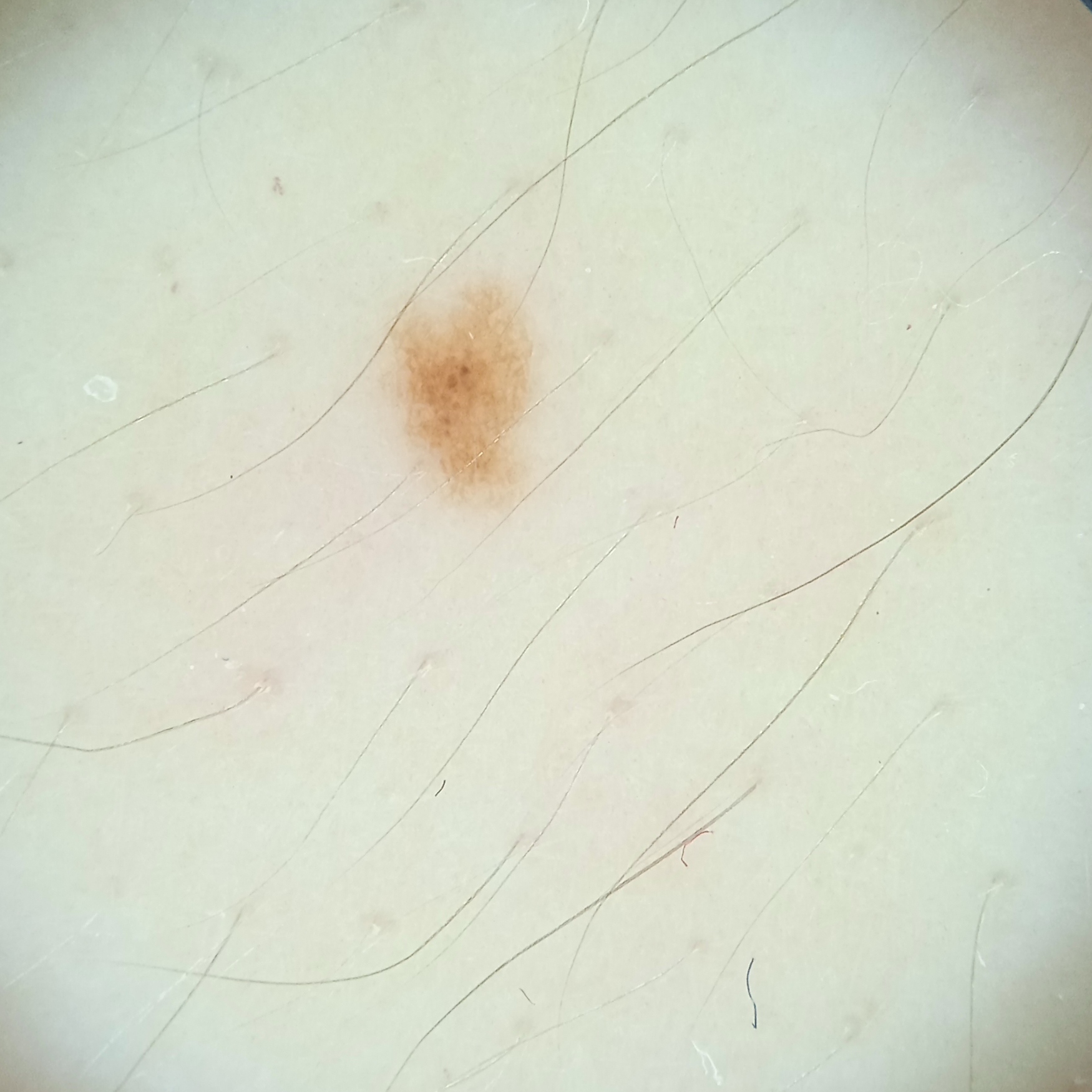Dermoscopy of a skin lesion.
A female subject 20 years of age.
The lesion involves an arm.
The consensus diagnosis for this lesion was a melanocytic nevus.